The patient reports a prior organ transplant. The patient describes having few moles overall. The patient says their skin reddens with sun exposure. A dermoscopy image of a skin lesion. Collected as part of a research study, without a referral diagnosis:
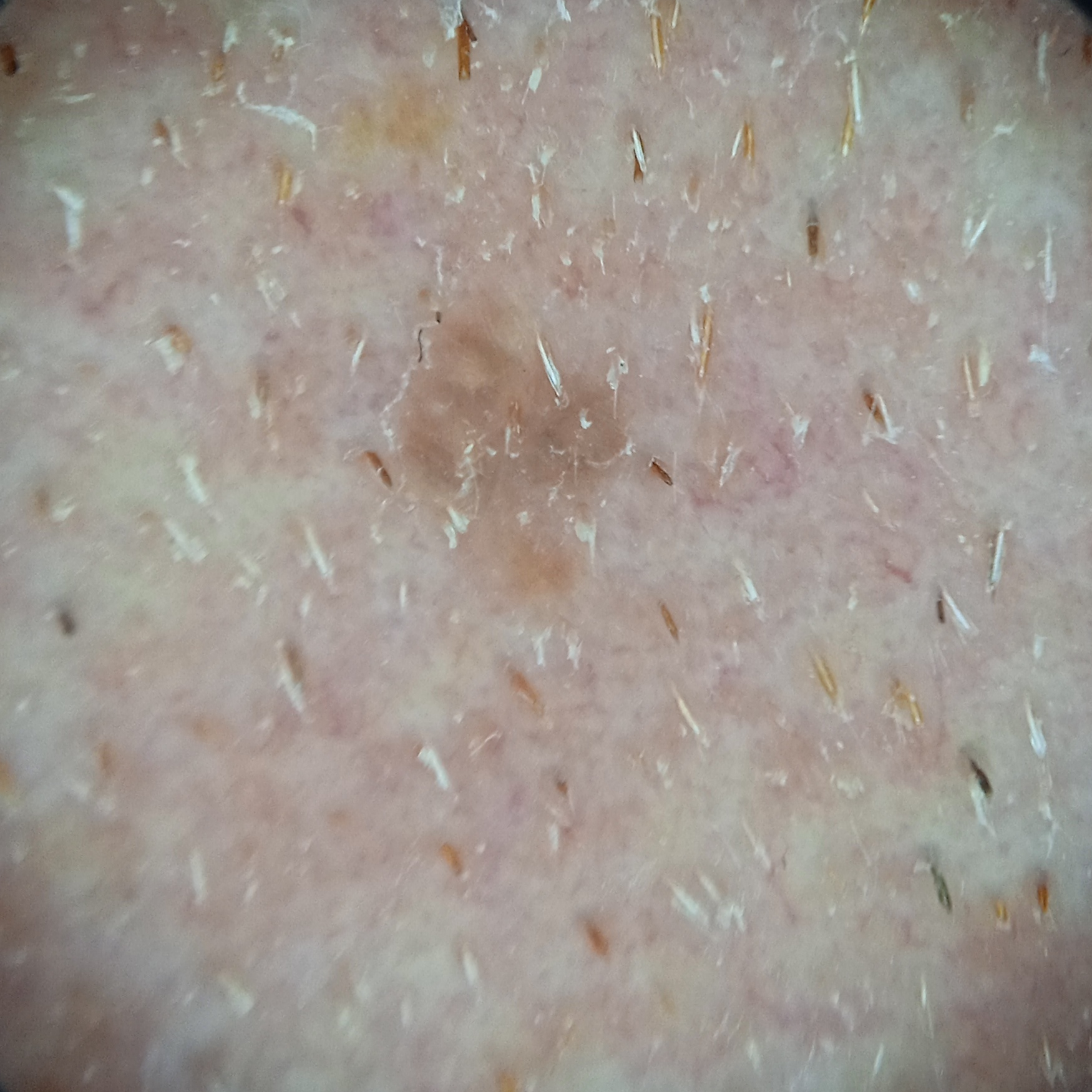Located on the face. The lesion measures approximately 3 mm. The lesion was assessed as a seborrheic keratosis.